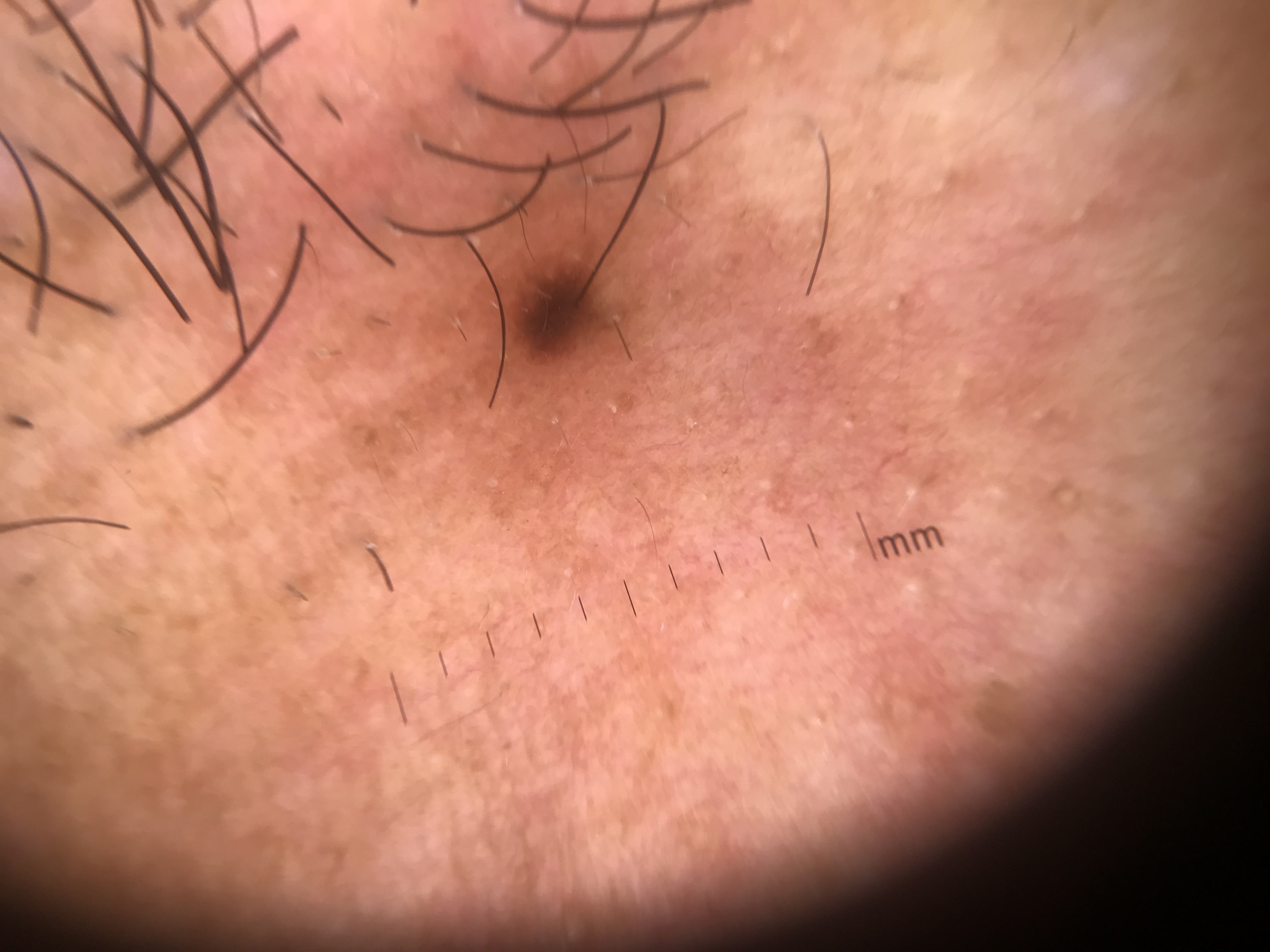Case:
- diagnostic label: junctional nevus (expert consensus)